Texture is reported as raised or bumpy · the affected area is the leg and arm · the patient considered this a rash · the photograph was taken at a distance: 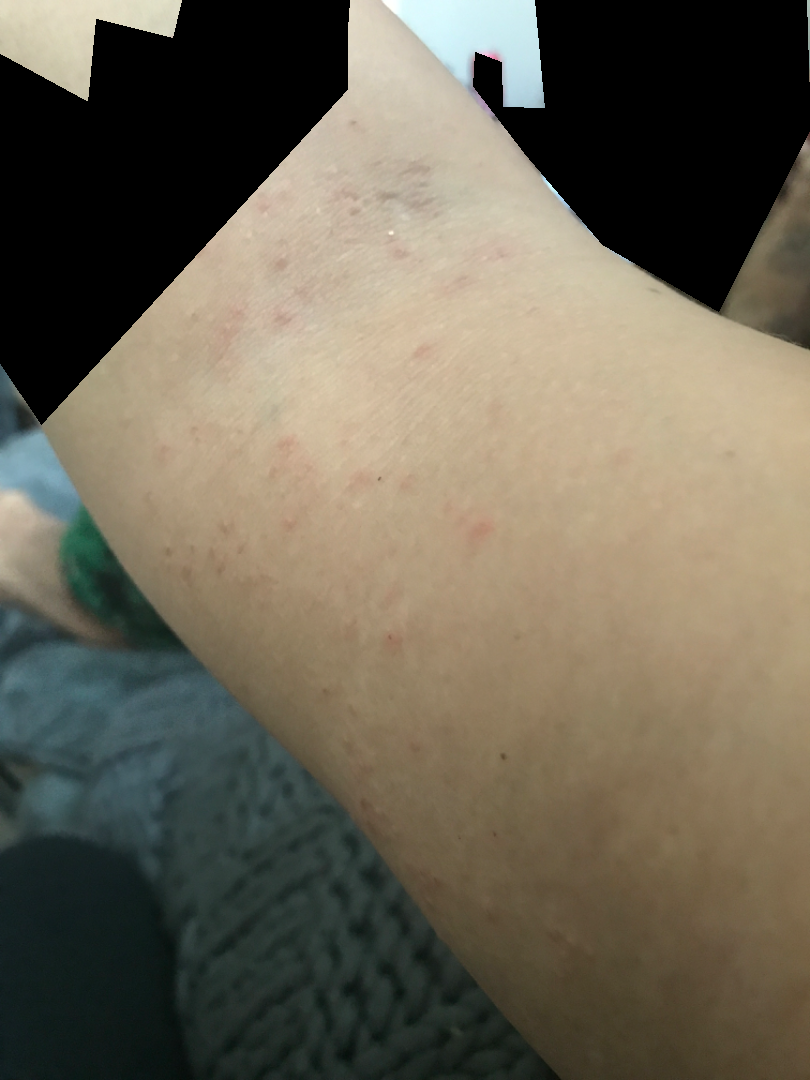The reviewer's impression was Eczema.